A female patient aged 28 to 32; a skin lesion imaged with contact-polarized dermoscopy — 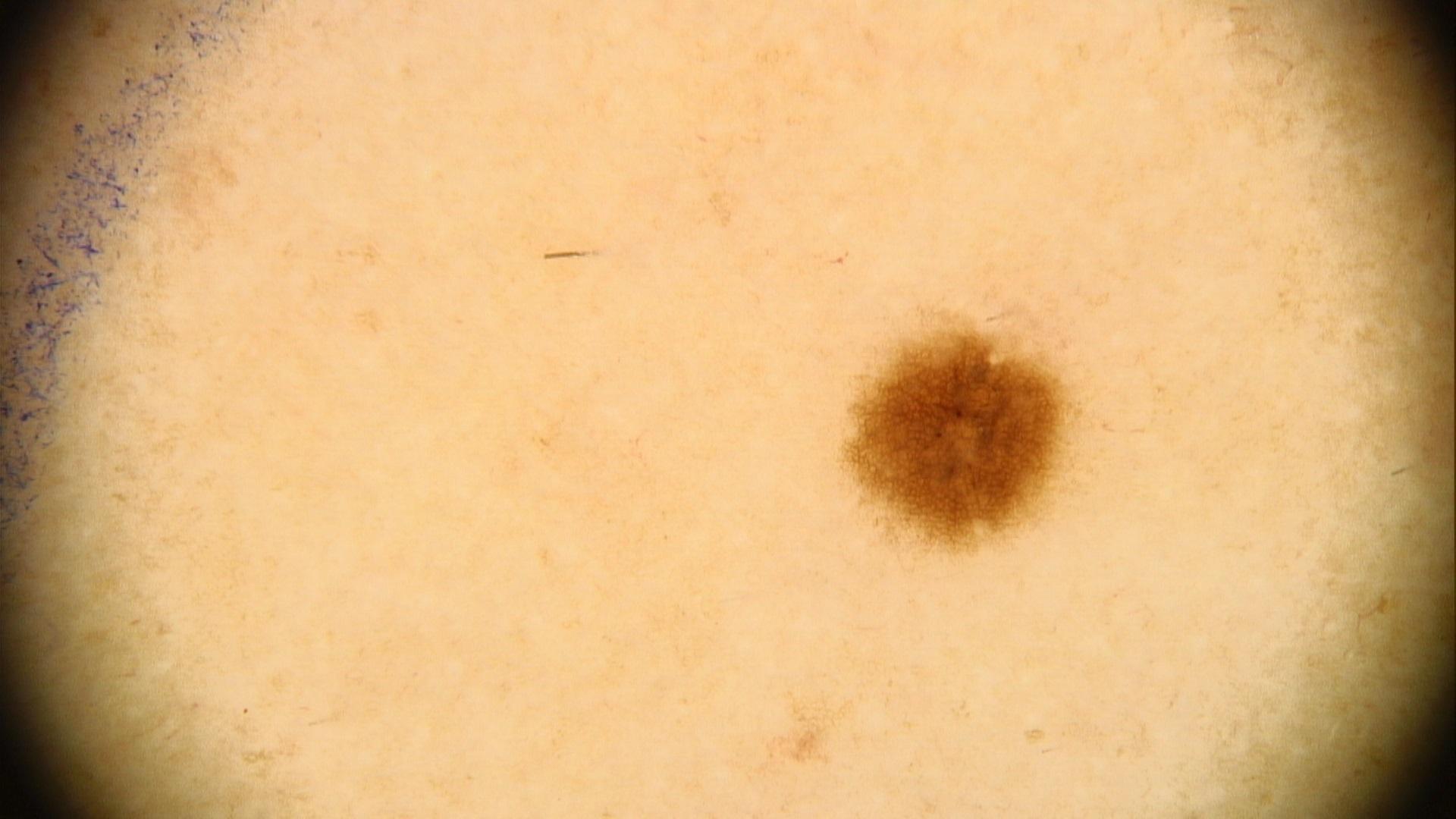anatomic site: a lower extremity, impression: Nevus.